Close-up view, the lesion involves the leg, the patient is a male aged 18–29:
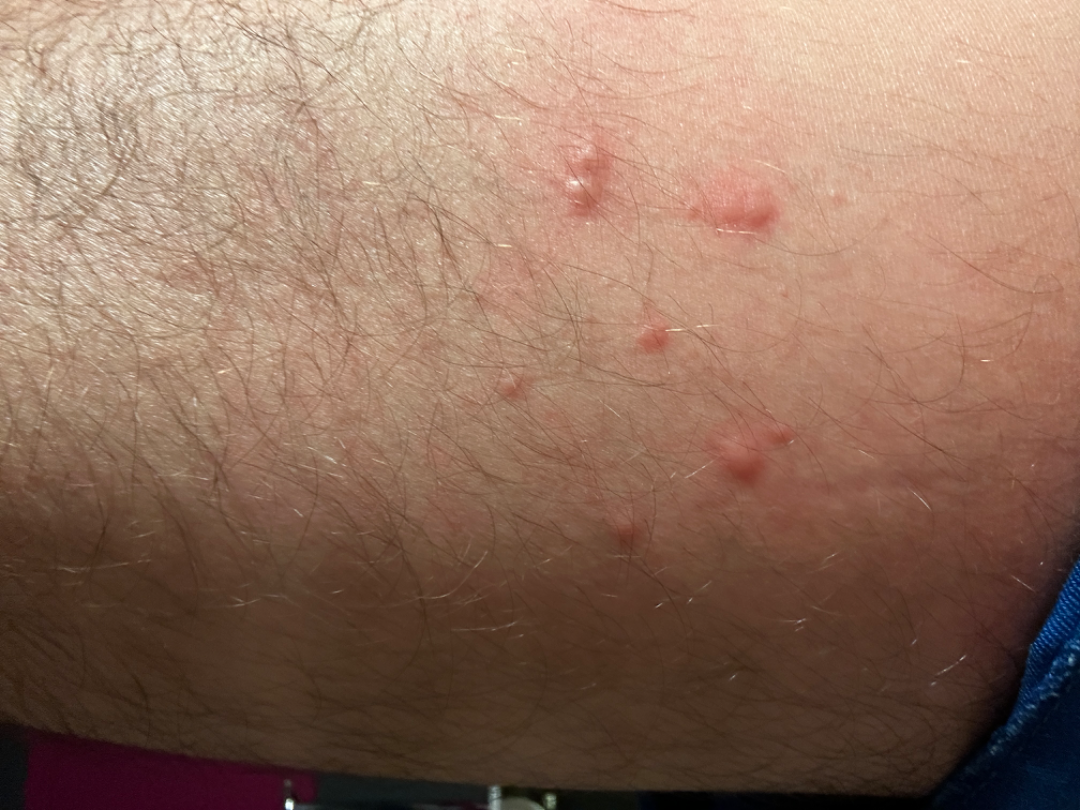{
  "differential": {
    "tied_lead": [
      "Folliculitis",
      "Herpes Zoster",
      "Allergic Contact Dermatitis"
    ]
  }
}